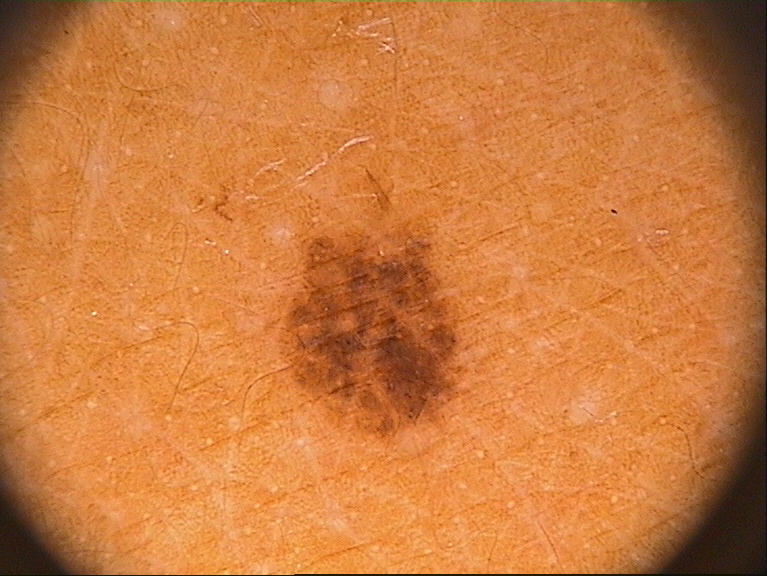A dermoscopic close-up of a skin lesion. As (left, top, right, bottom), the lesion spans <box>273, 223, 475, 446</box>. Consistent with a melanocytic nevus, a benign lesion.